This is a close-up image: 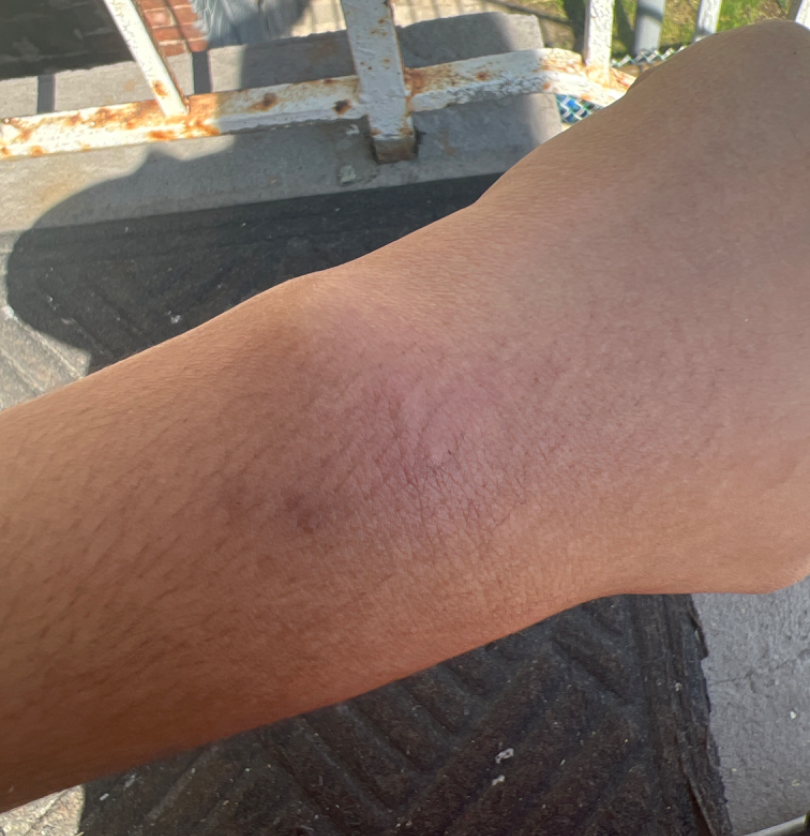{
  "differential": {
    "leading": [
      "Allergic Contact Dermatitis"
    ],
    "considered": [
      "Irritant Contact Dermatitis"
    ]
  }
}